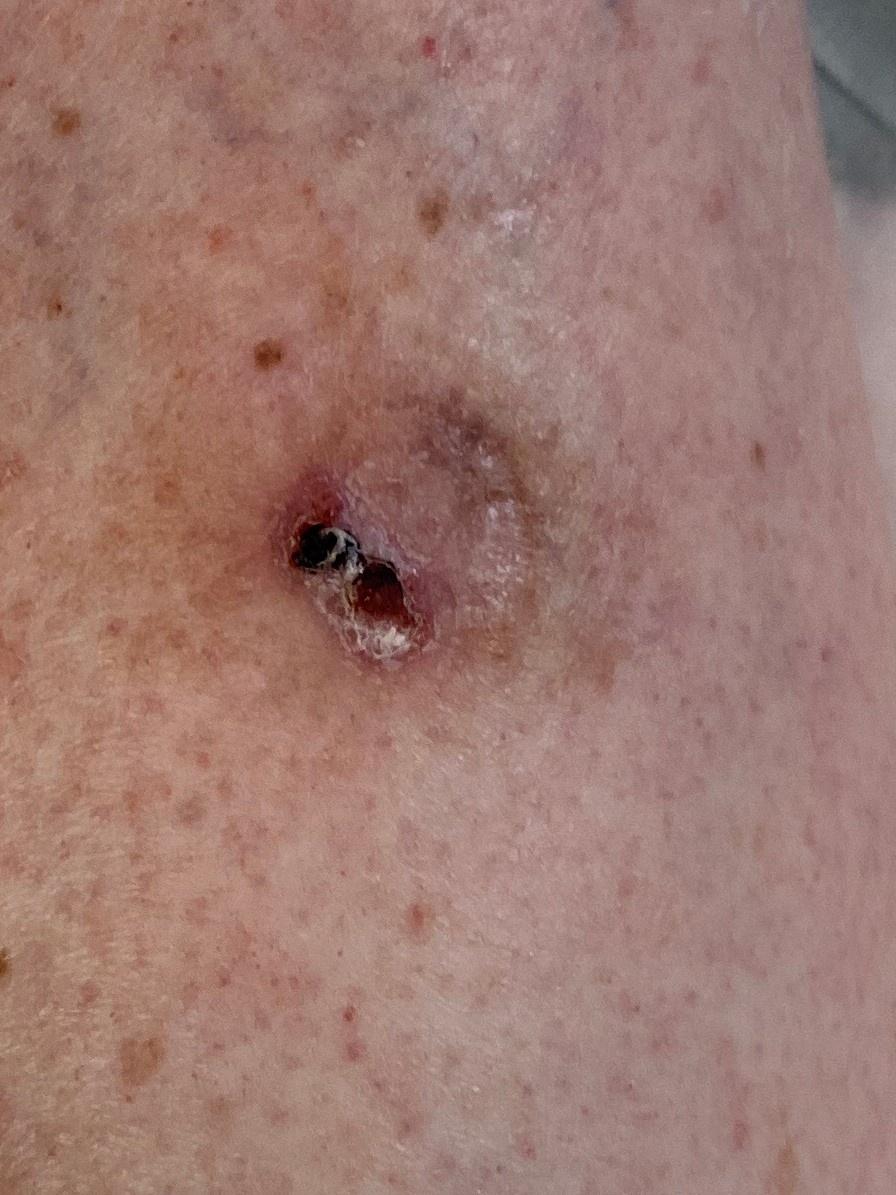Histopathologically confirmed as a basal cell carcinoma.